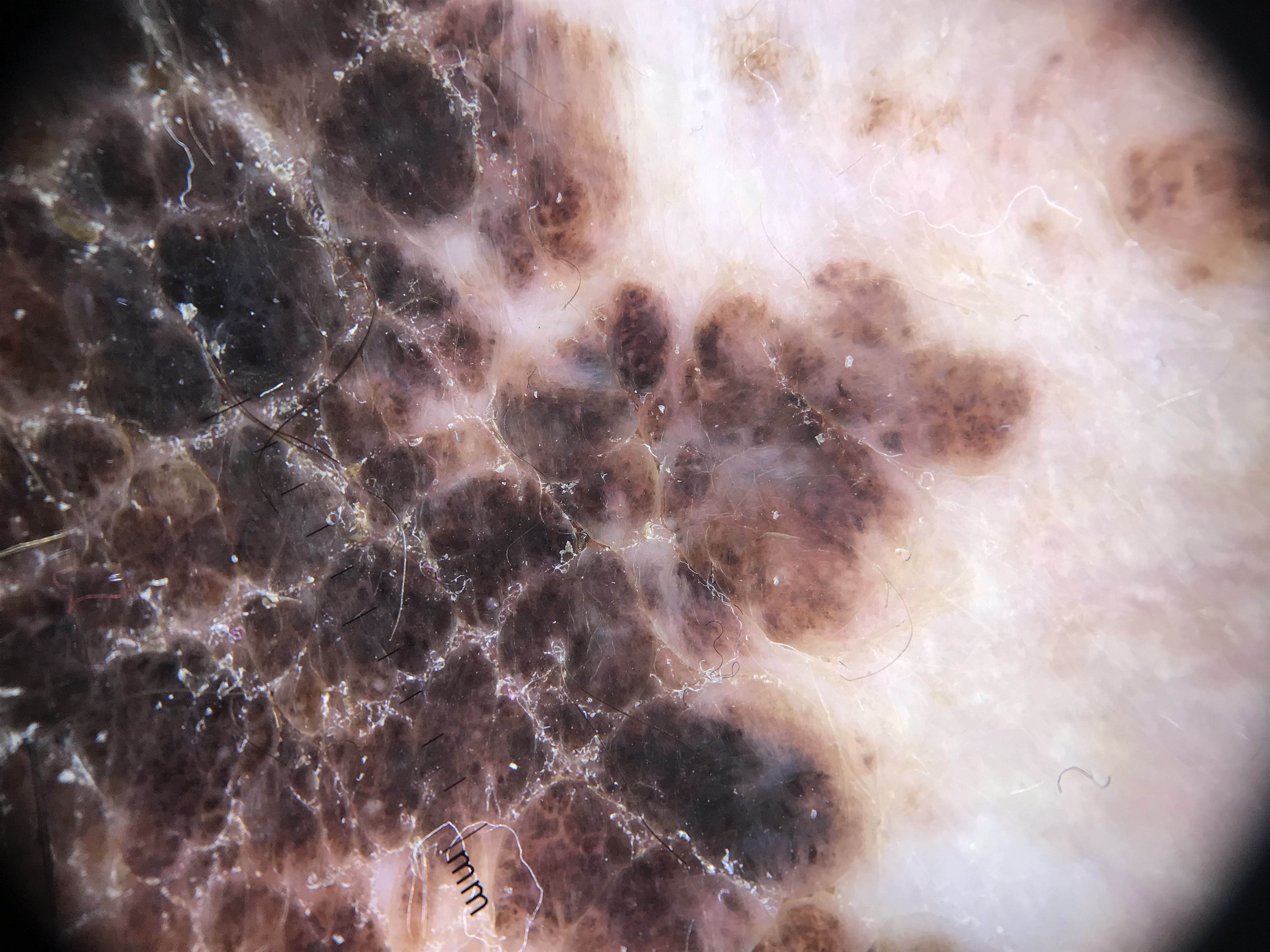<case>
  <lesion_type>
    <main_class>banal</main_class>
    <pattern>compound</pattern>
  </lesion_type>
  <diagnosis>
    <name>congenital compound nevus</name>
    <code>ccb</code>
    <malignancy>benign</malignancy>
    <super_class>melanocytic</super_class>
    <confirmation>expert consensus</confirmation>
  </diagnosis>
</case>